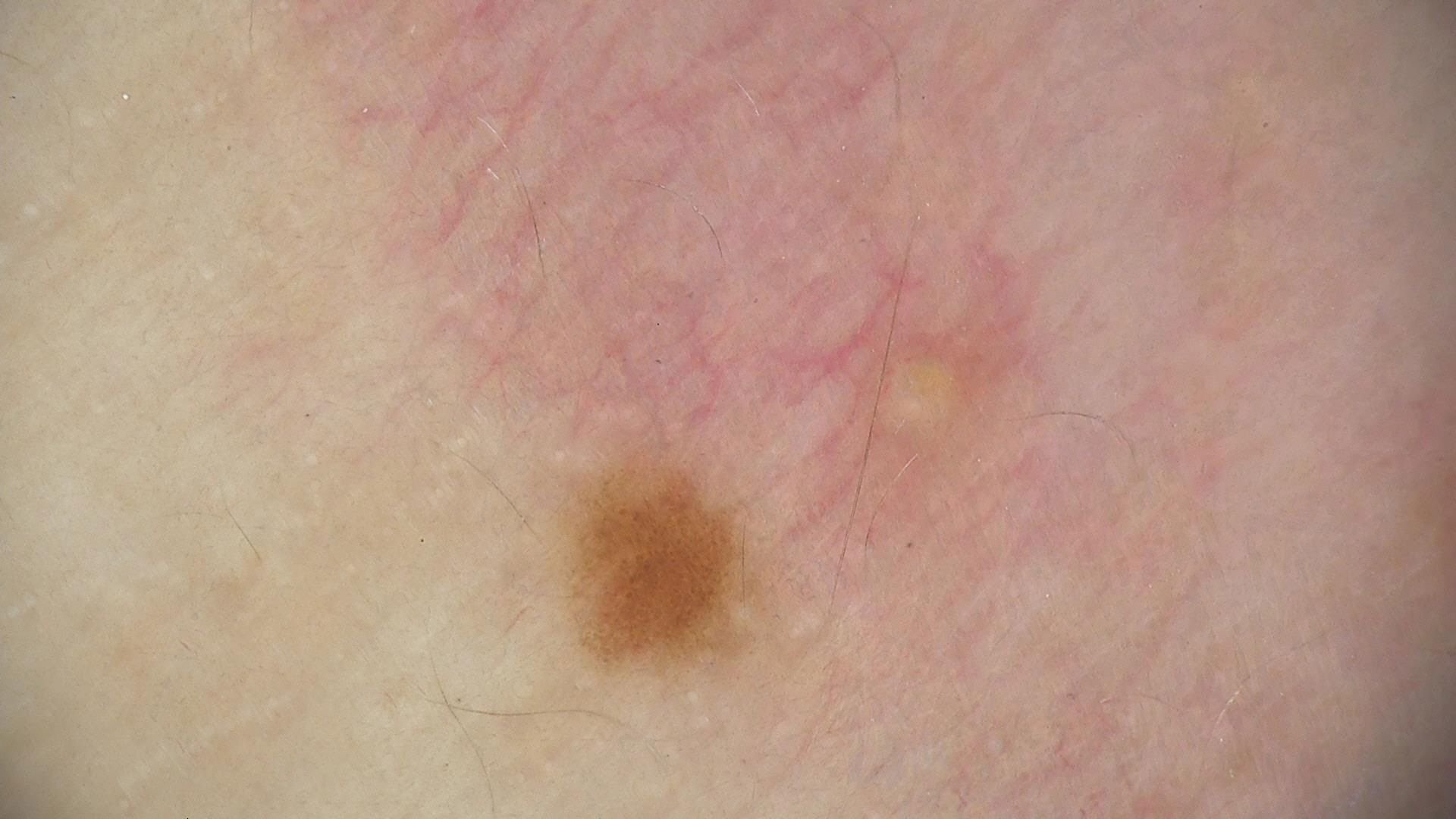label — junctional nevus (expert consensus).